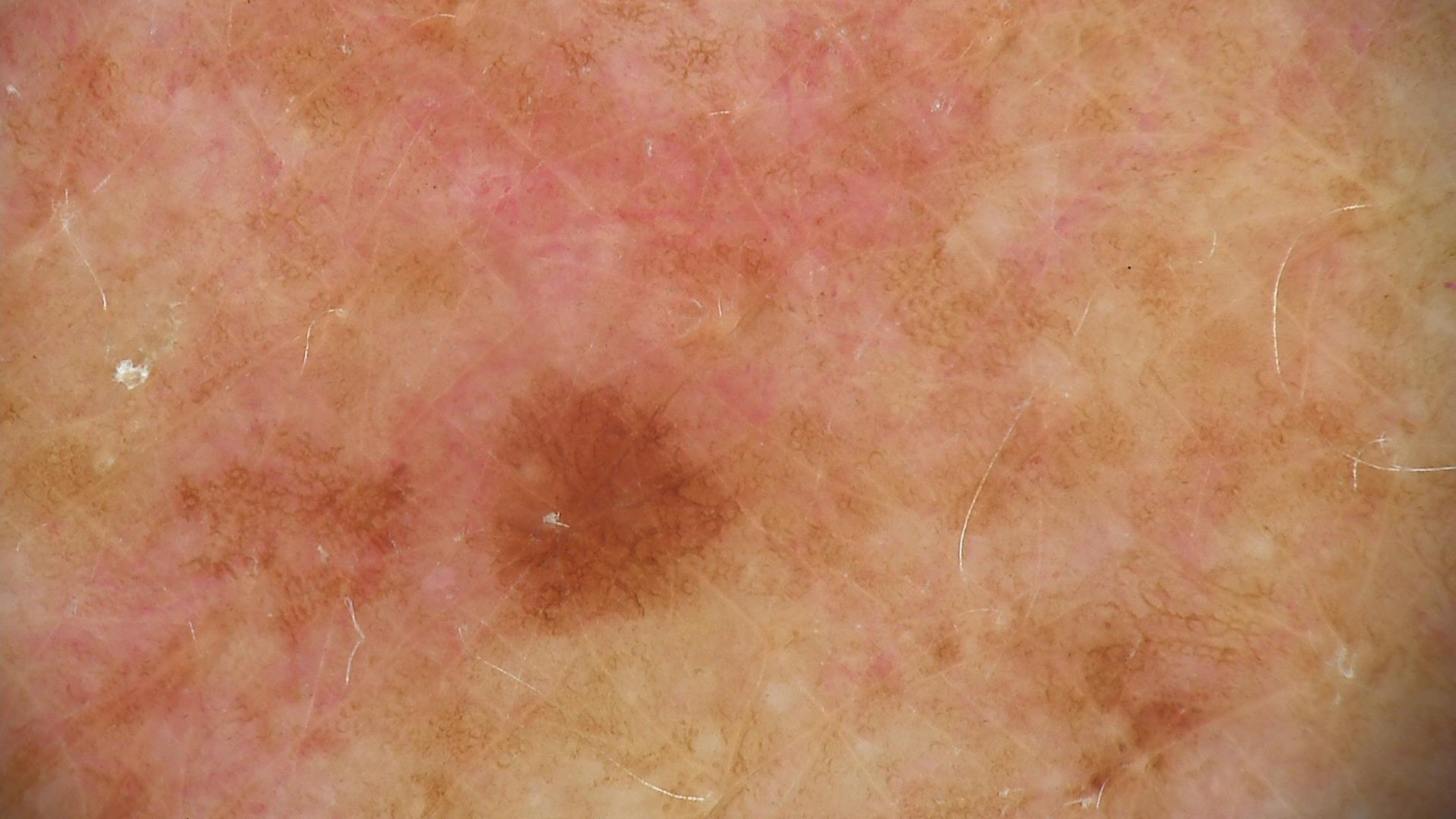Case:
A dermoscopic photograph of a skin lesion.
Conclusion:
The diagnostic label was a dysplastic junctional nevus.